The condition has been present for about one day, the contributor reports the lesion is flat, the patient described the issue as a nail problem, the contributor reports associated fatigue and joint pain, this is a close-up image, the affected area is the leg, the subject is a male aged 50–59: 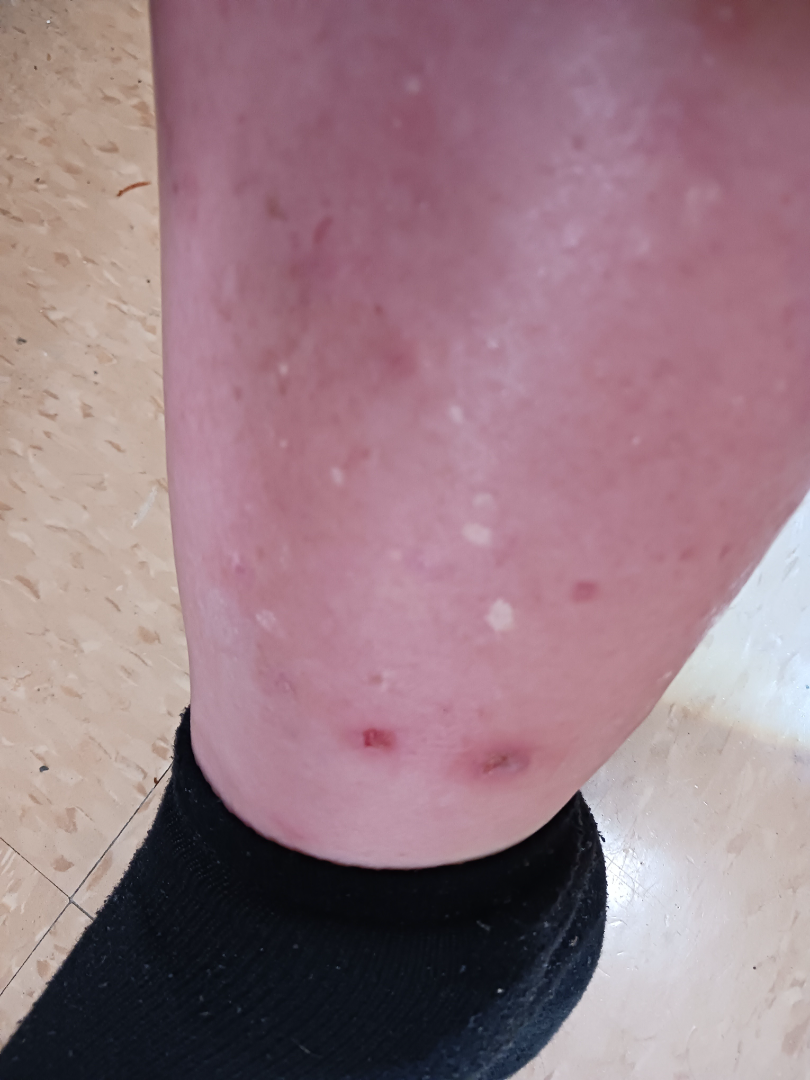The dermatologist could not determine a likely condition from the photograph alone.